A dermoscopy image of a single skin lesion:
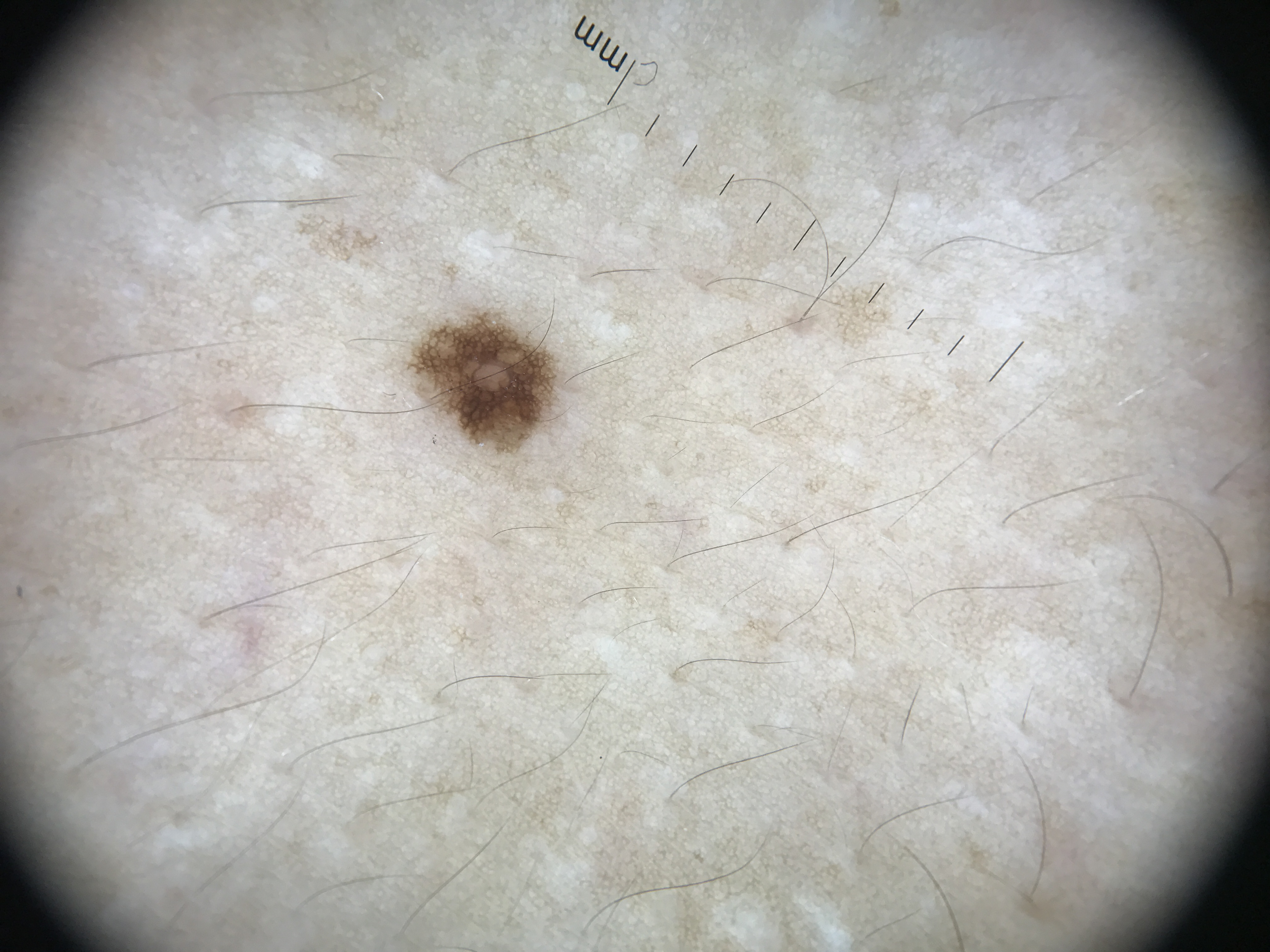Diagnosed as a benign lesion — a dysplastic junctional nevus.